Collected as part of a research study, without a referral diagnosis.
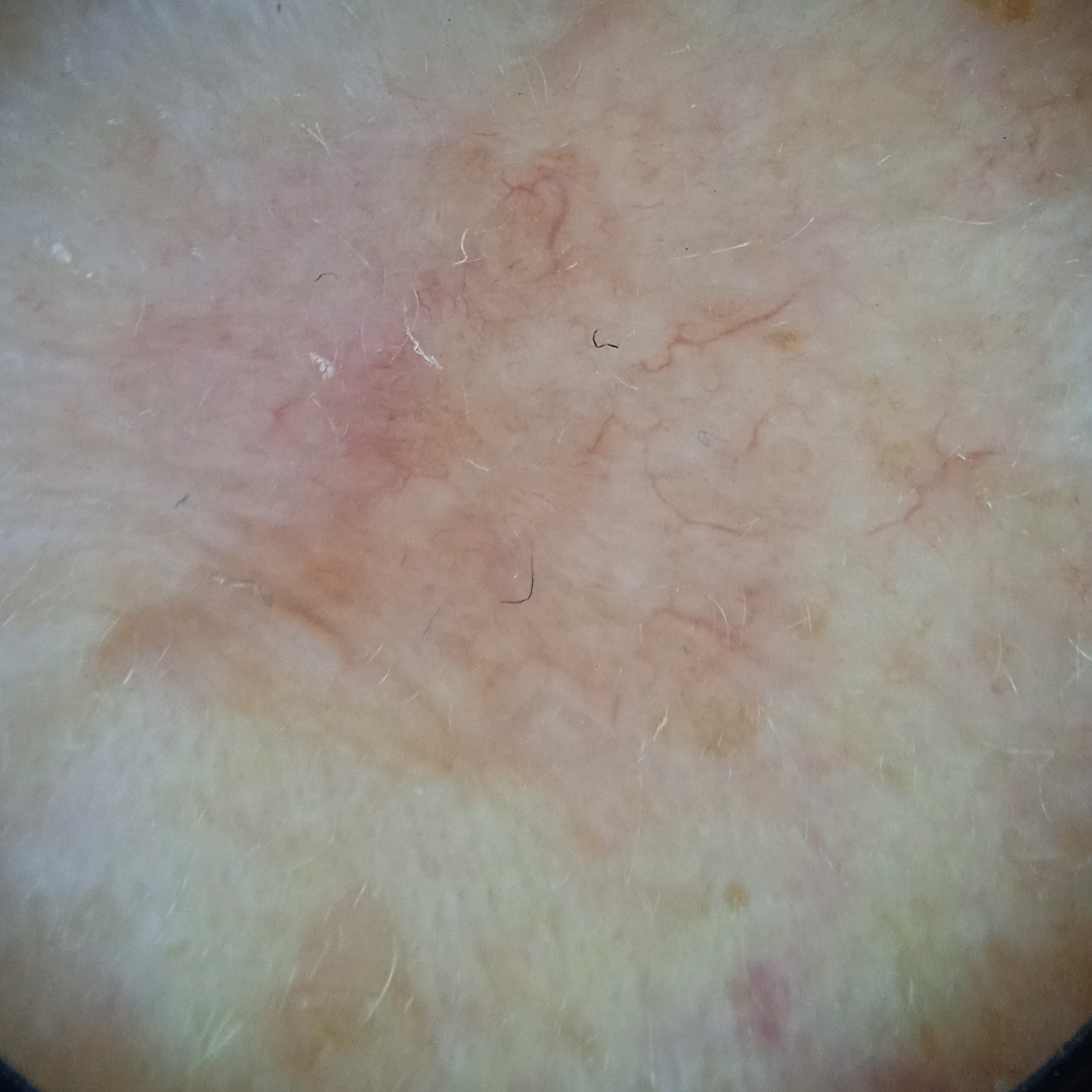Located on the face. Measuring roughly 8.2 mm. The lesion was assessed as a basal cell carcinoma.